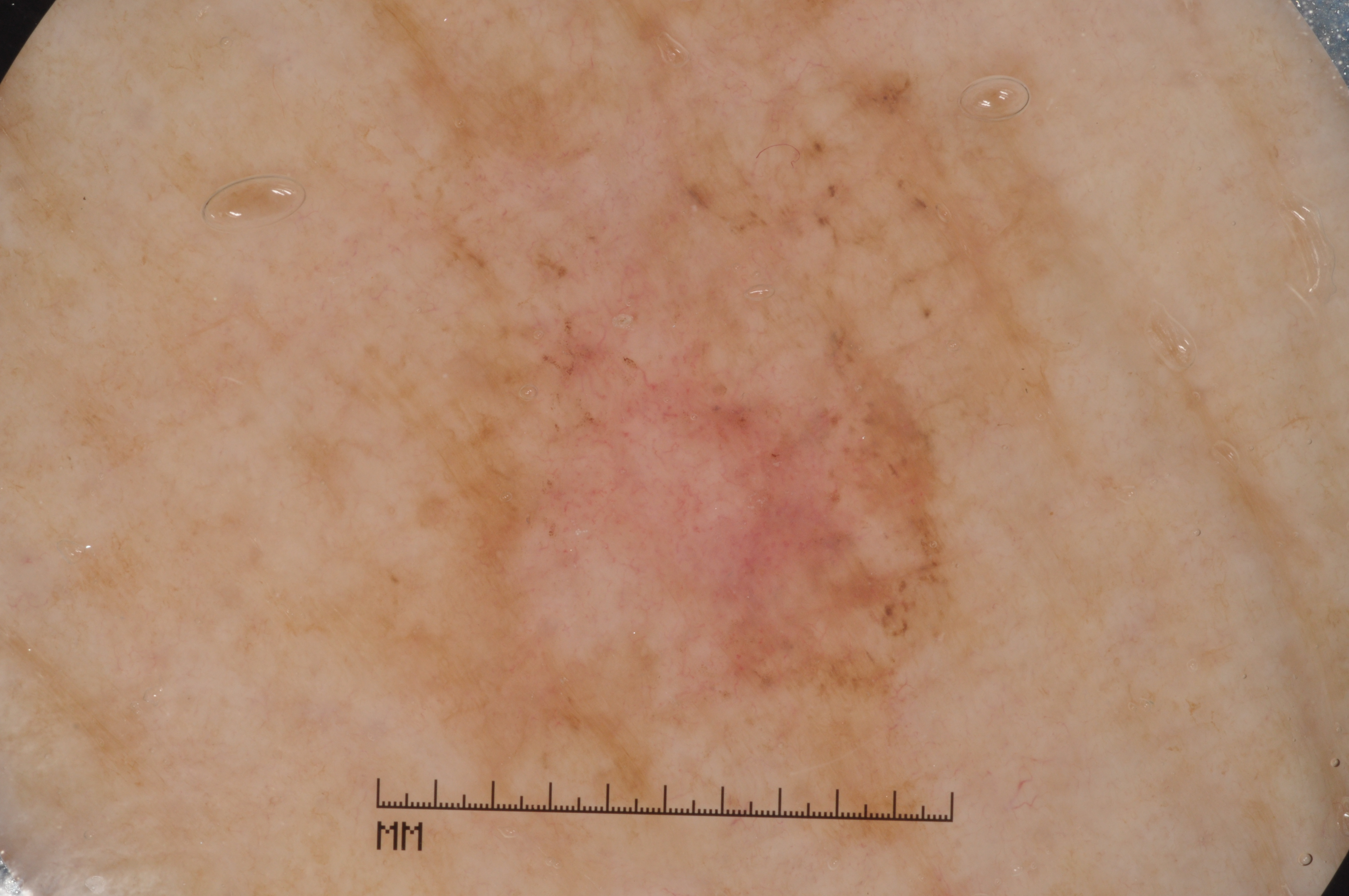  patient:
    sex: female
    age_approx: 80
  image:
    modality: dermoscopy
  dermoscopic_features:
    present:
      - pigment network
      - milia-like cysts
    absent:
      - streaks
      - negative network
  lesion_location:
    bbox_xyxy:
      - 289
      - 1
      - 1097
      - 853
  diagnosis:
    name: melanoma
    malignancy: malignant
    lineage: melanocytic
    provenance: histopathology